The referring clinician suspected melanoma; a female patient 50 years of age; a clinical photograph showing a skin lesion; a moderate number of moles by the patient's own estimate; the patient says their skin reddens painfully with sun exposure; the patient reports no personal history of cancer — 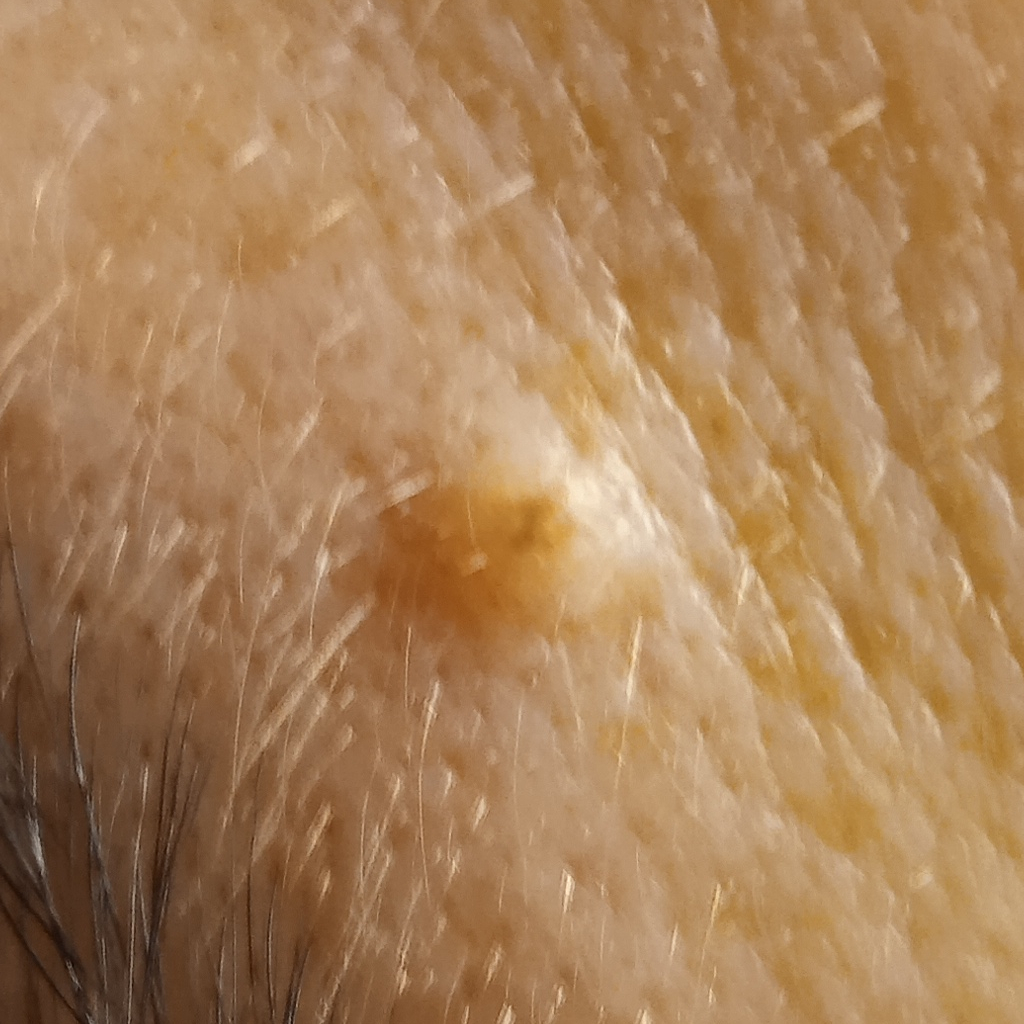| feature | finding |
|---|---|
| location | the face |
| assessment | melanocytic nevus (dermatologist consensus) |